The patient reports the lesion is fluid-filled. The affected area is the leg and arm. Skin tone: Fitzpatrick III. This is a close-up image. Reported duration is less than one week. The patient reports bothersome appearance, itching, pain and burning. The contributor is a female aged 40–49 — 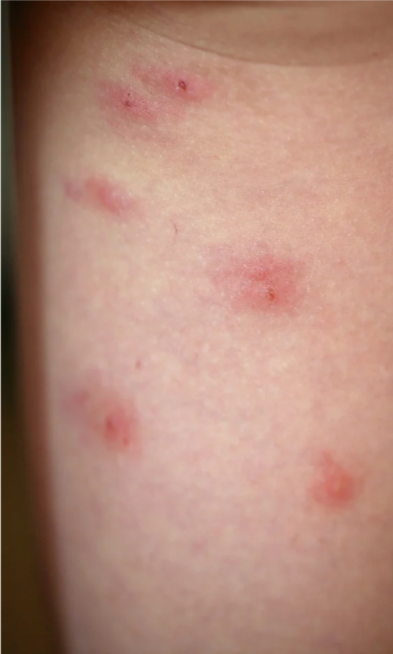A single dermatologist reviewed the case: most consistent with Insect Bite.